By history, tobacco use, prior skin cancer (patient or family), prior malignancy (patient or family), alcohol use, and pesticide exposure · recorded as skin type III · a clinical close-up photograph of a skin lesion — 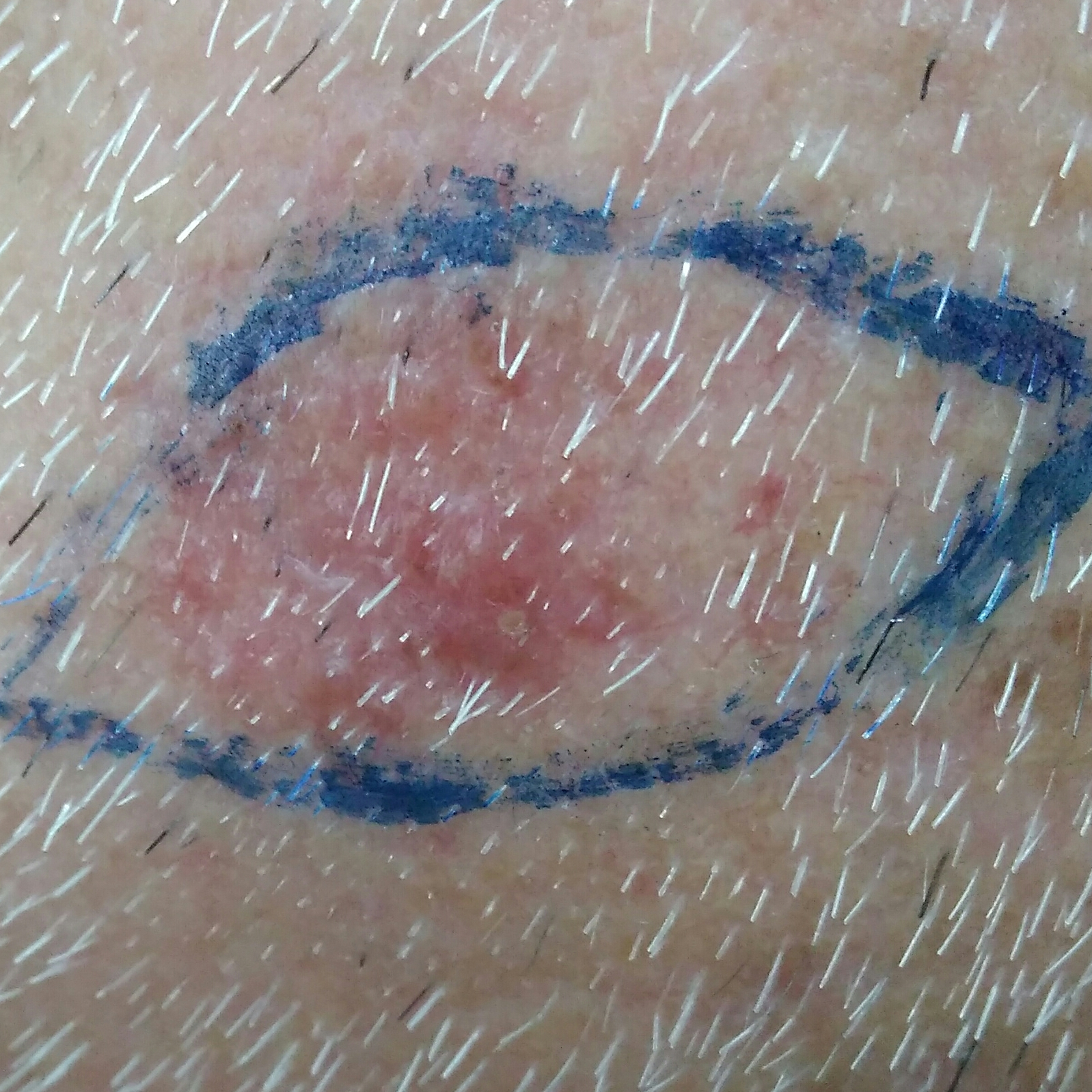The lesion is on the face.
The lesion measures approximately 12 × 9 mm.
Per patient report, the lesion is elevated.
Biopsy-confirmed as a malignancy — a basal cell carcinoma.